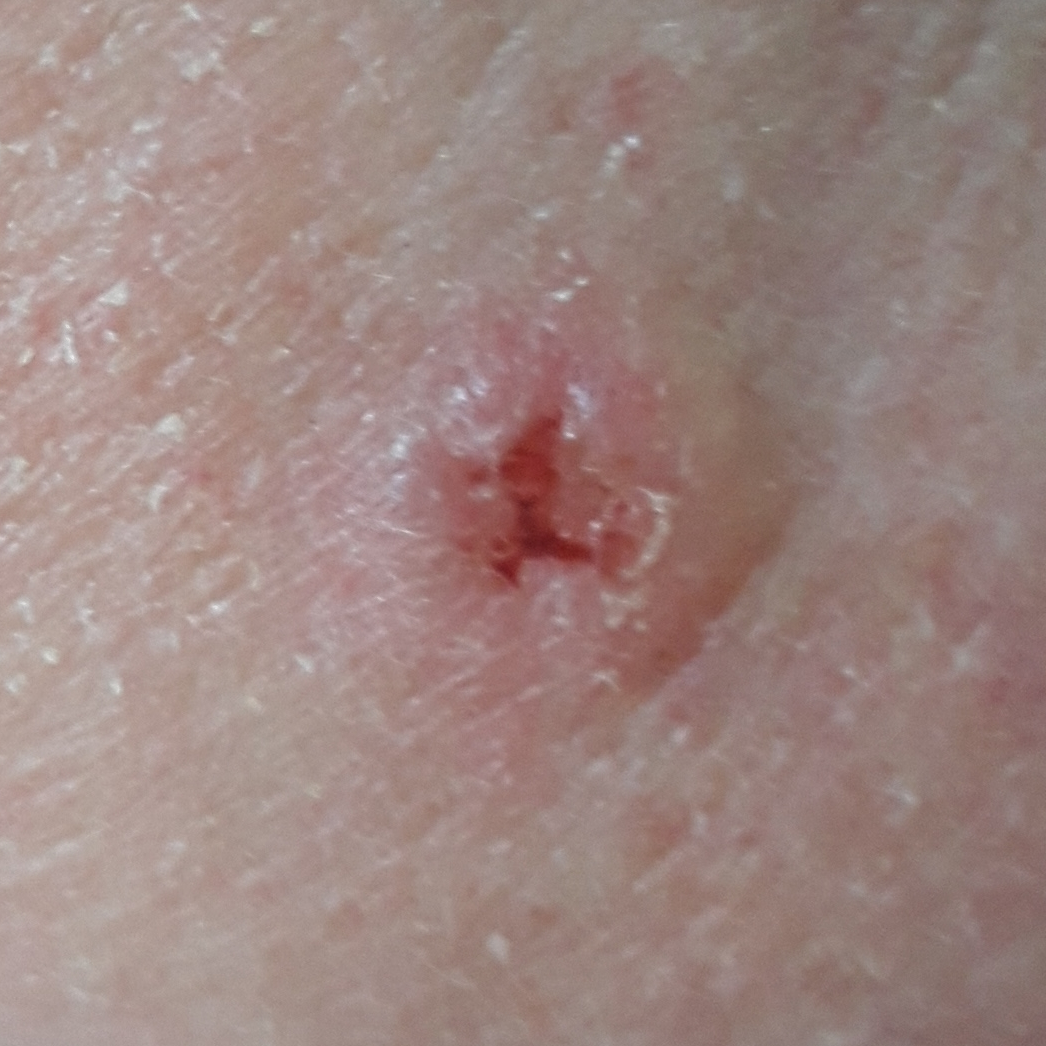Histopathology confirmed a basal cell carcinoma.